Symptoms reported: itching; located on the head or neck; close-up view; the lesion is described as raised or bumpy; present for about one day: 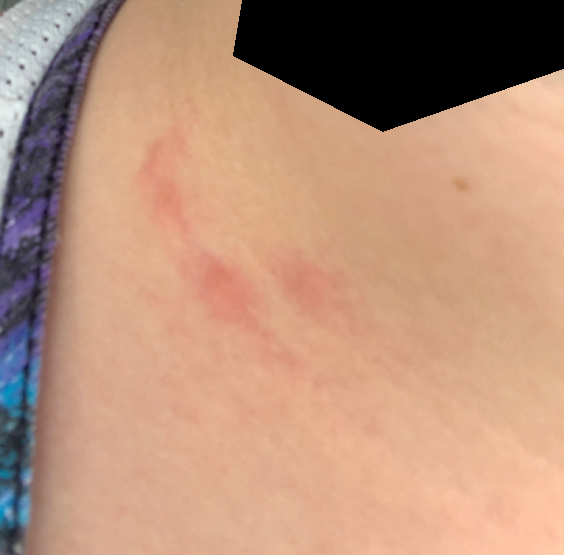Findings: The reviewing dermatologist was unable to assign a differential diagnosis from the image.